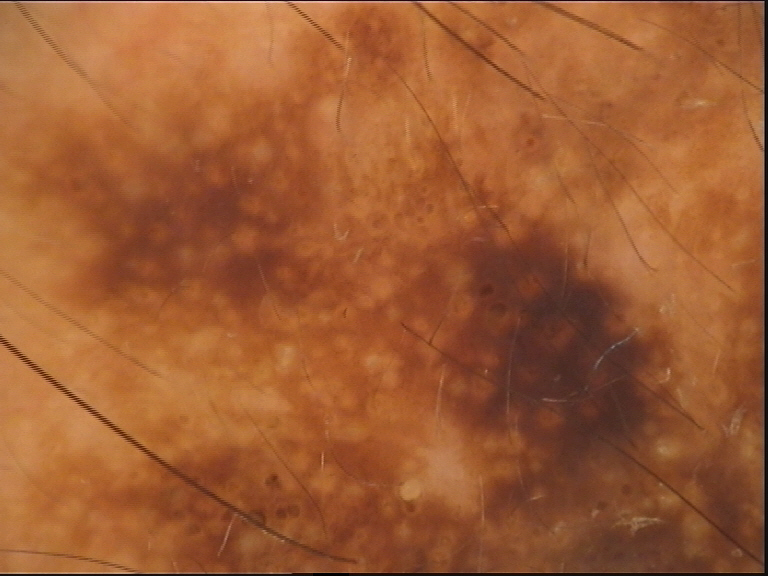This is a keratinocytic lesion.
Labeled as a benign lesion — a seborrheic keratosis.